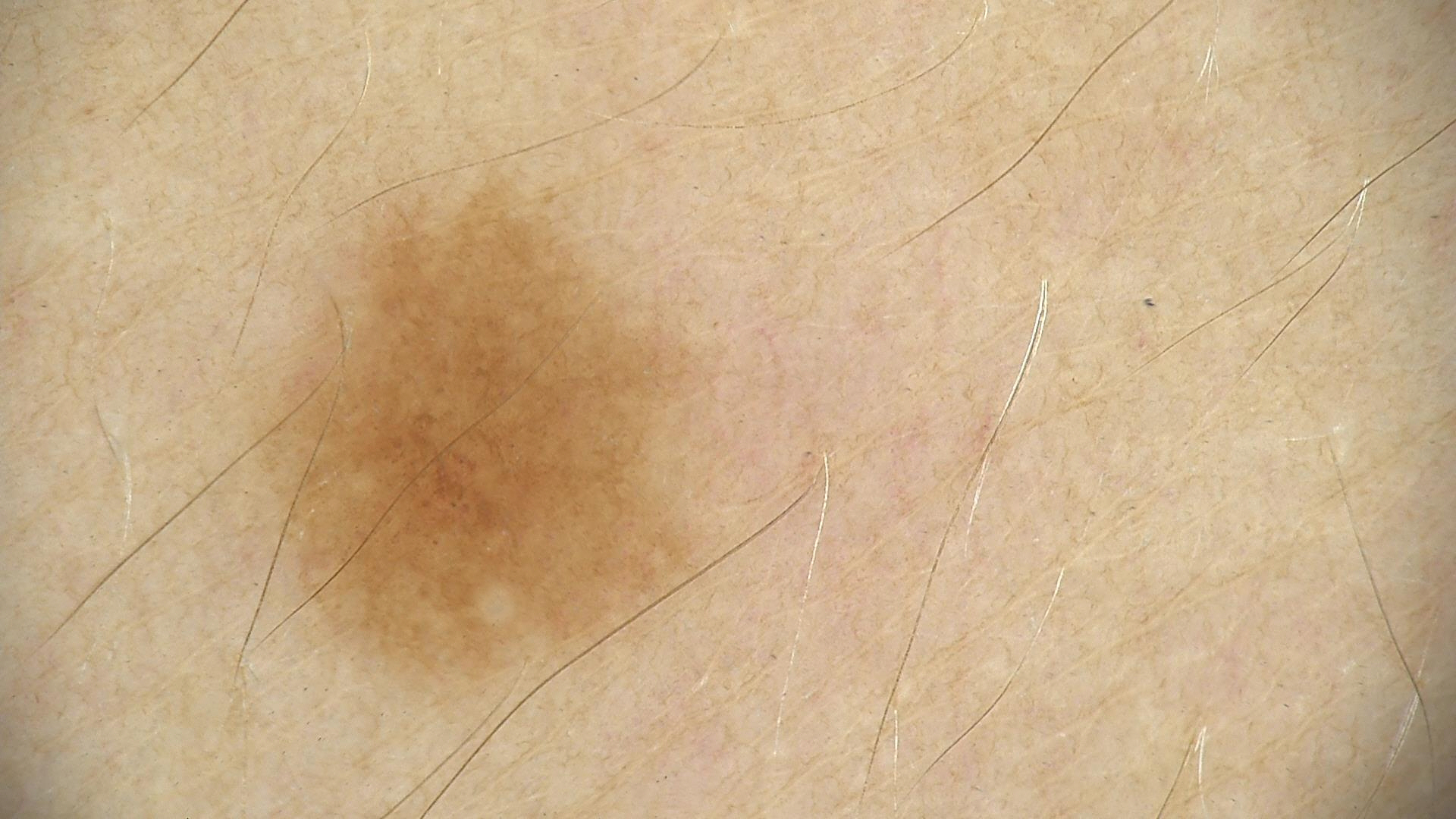Consistent with a dysplastic junctional nevus.